The condition has been present for about one day. The arm is involved. Fitzpatrick phototype III; non-clinician graders estimated Monk Skin Tone 2 or 3 (two reviewer pools). Texture is reported as raised or bumpy. Close-up view:
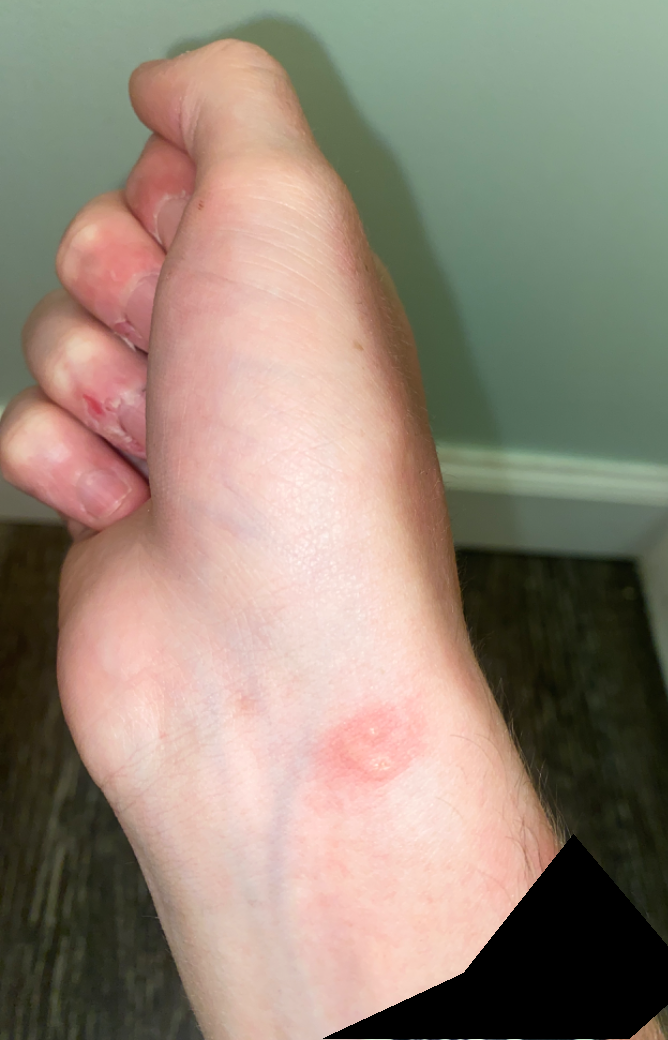• dermatologist impression — Eczema (0.50); Allergic Contact Dermatitis (0.50)